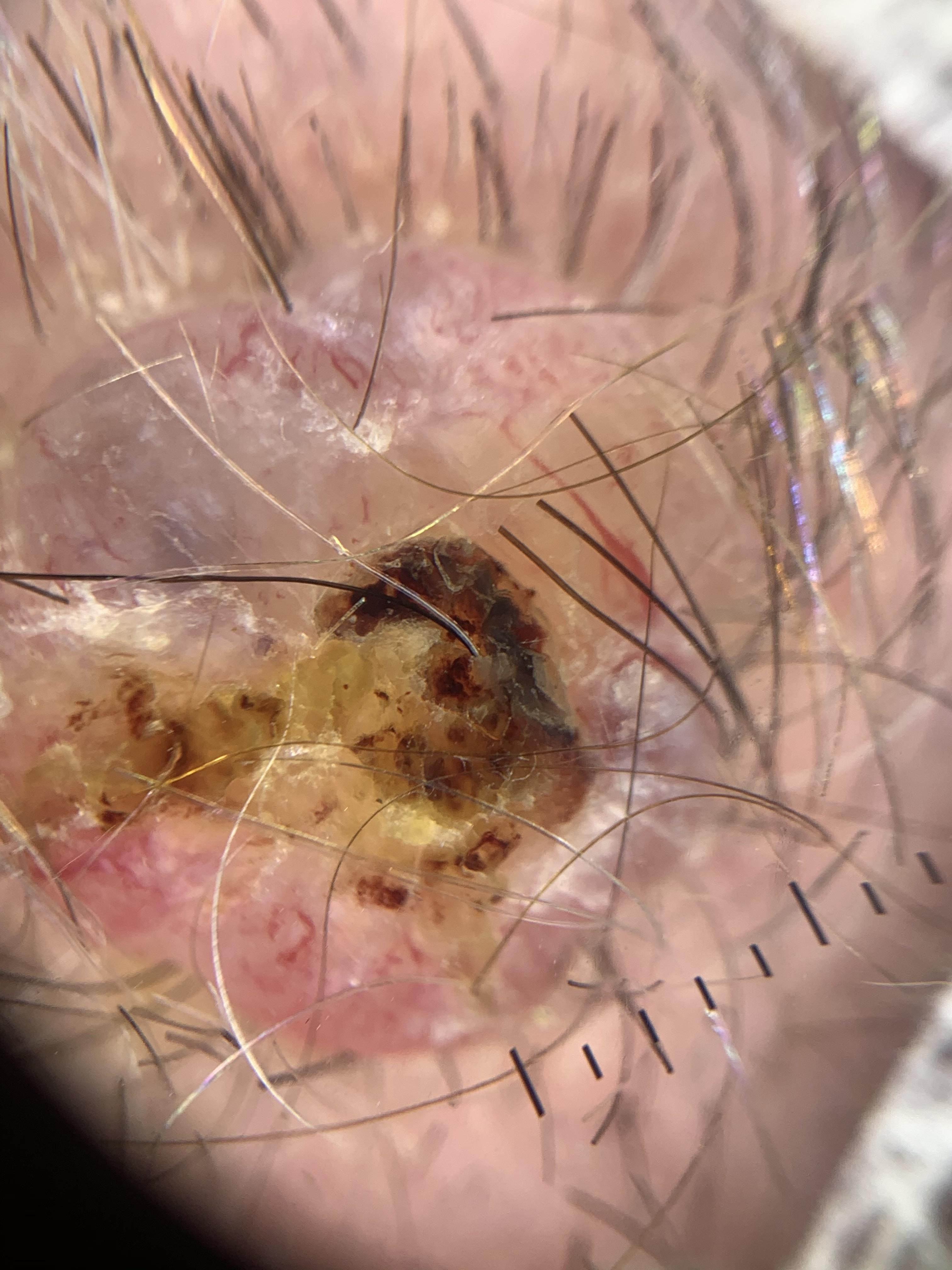Histopathological examination showed a basal cell carcinoma.